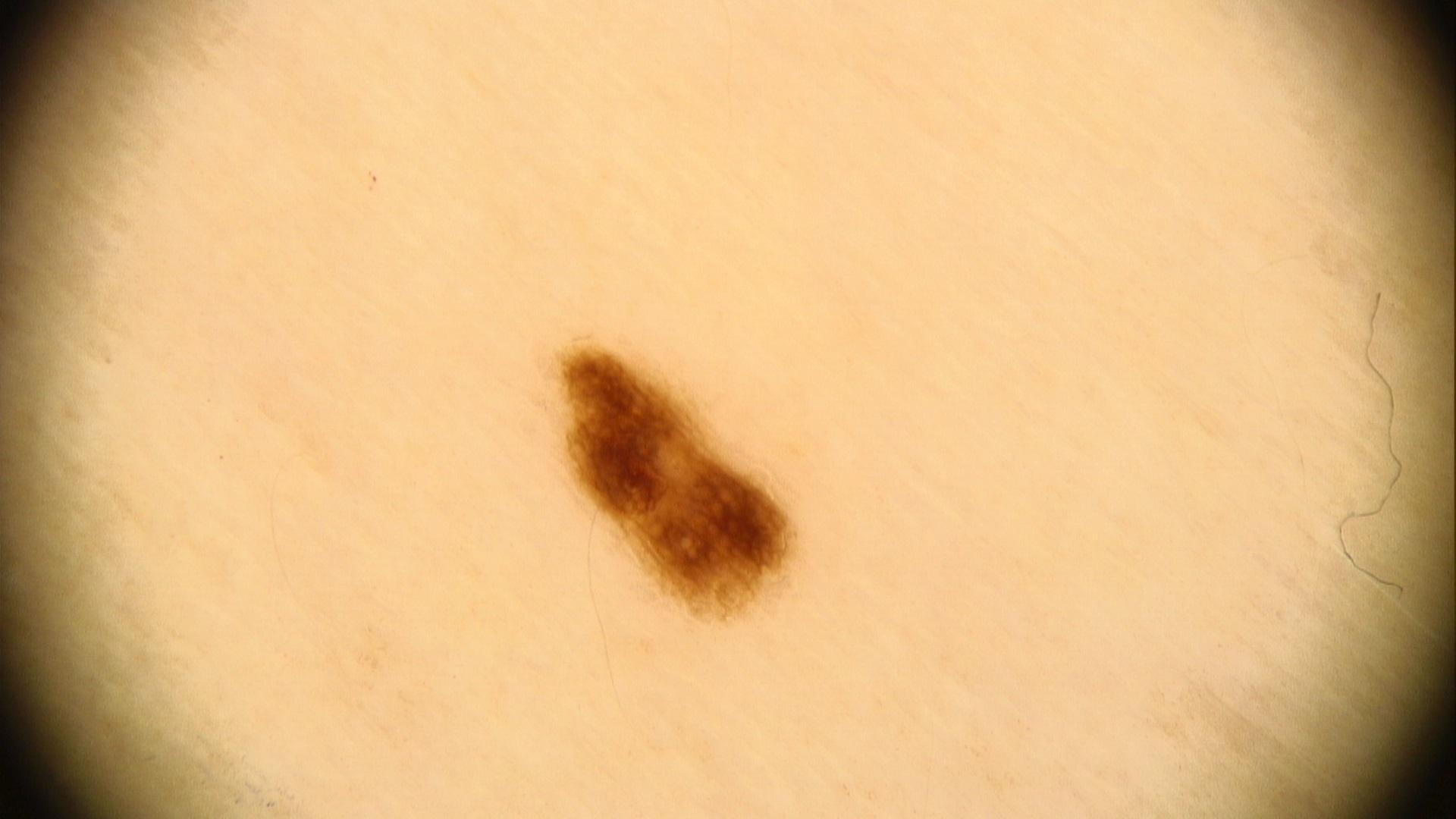Image and clinical context: A female patient in their mid-50s. A skin lesion imaged with contact-polarized dermoscopy. The lesion was found on a lower extremity. Conclusion: The clinical assessment was a nevus.